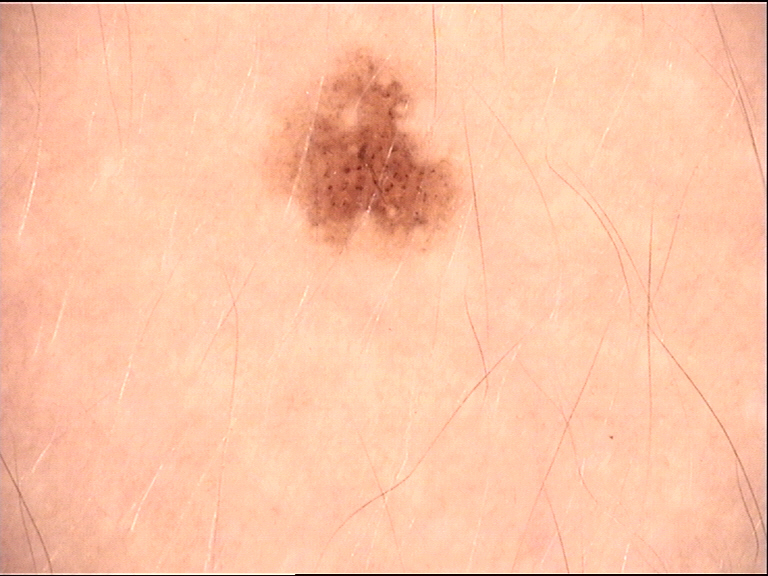A skin lesion imaged with a dermatoscope. Consistent with a dysplastic junctional nevus.